The lesion involves the top or side of the foot and leg. Present for less than one week. The photo was captured at a distance. The subject is 18–29, female. The patient considered this a rash:
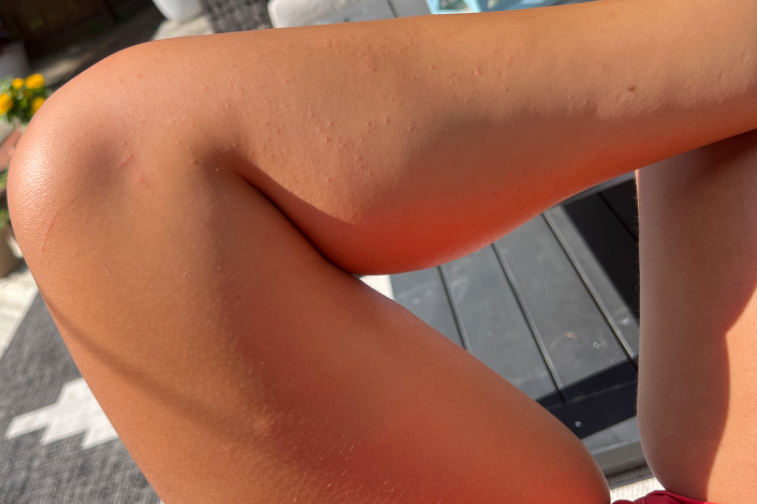Folliculitis (most likely).